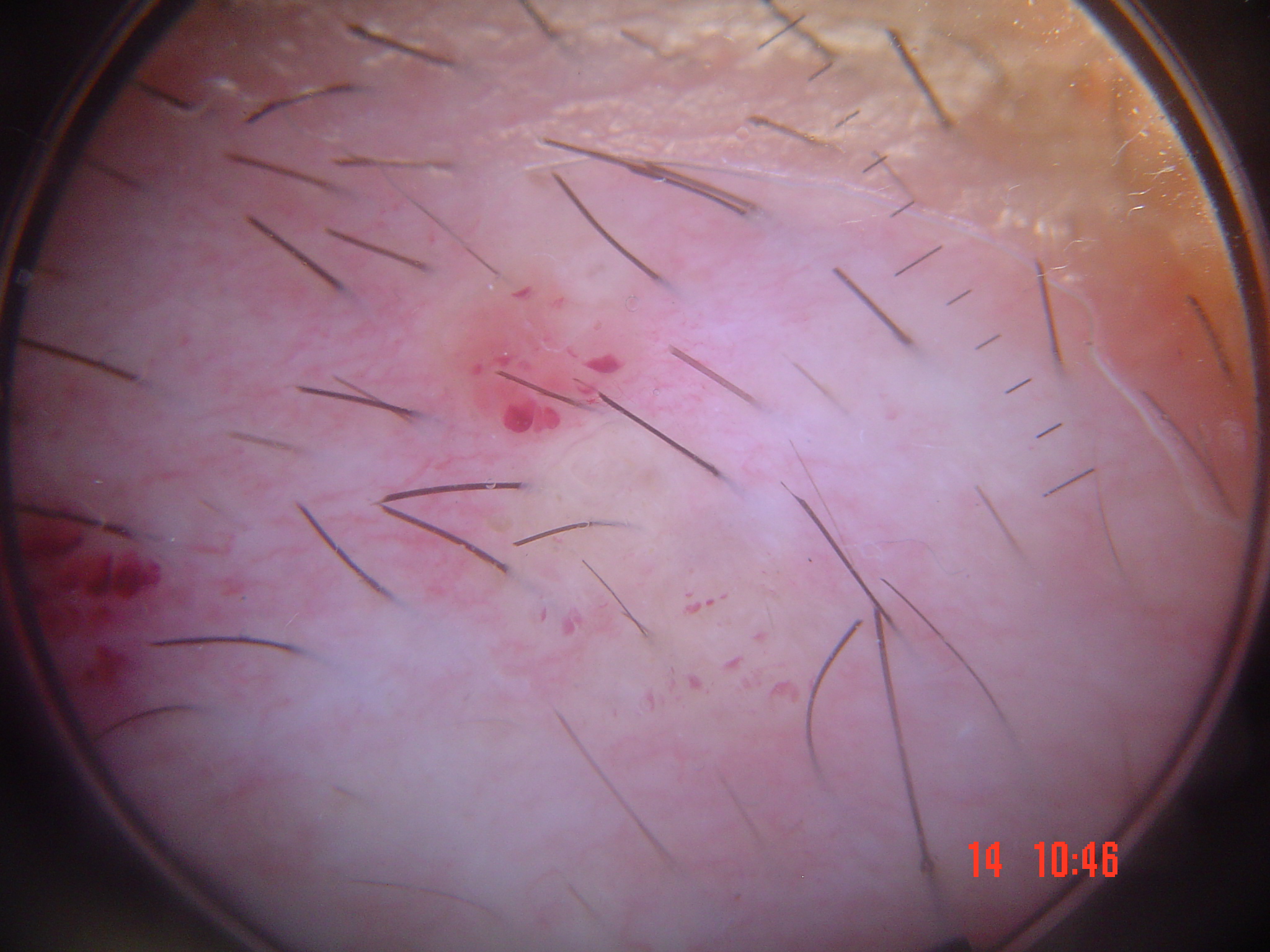Diagnosed as a lymphangioma.